A dermoscopic image of a skin lesion:
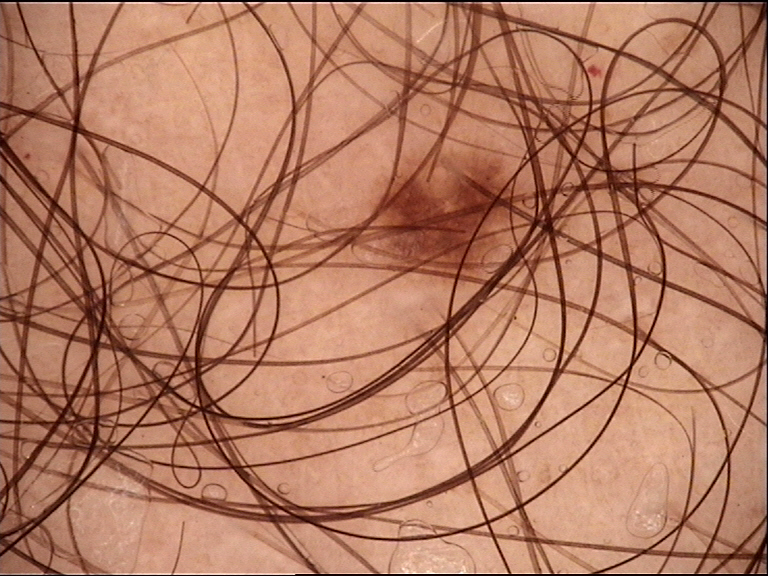class — dysplastic junctional nevus (expert consensus)